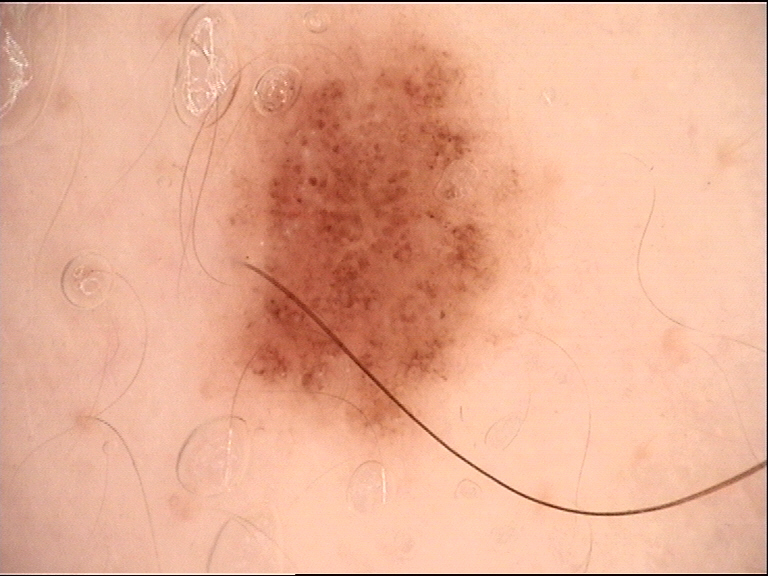The diagnostic label was a benign lesion — a dysplastic junctional nevus.